A clinical photograph showing a skin lesion · a subject age 59 — 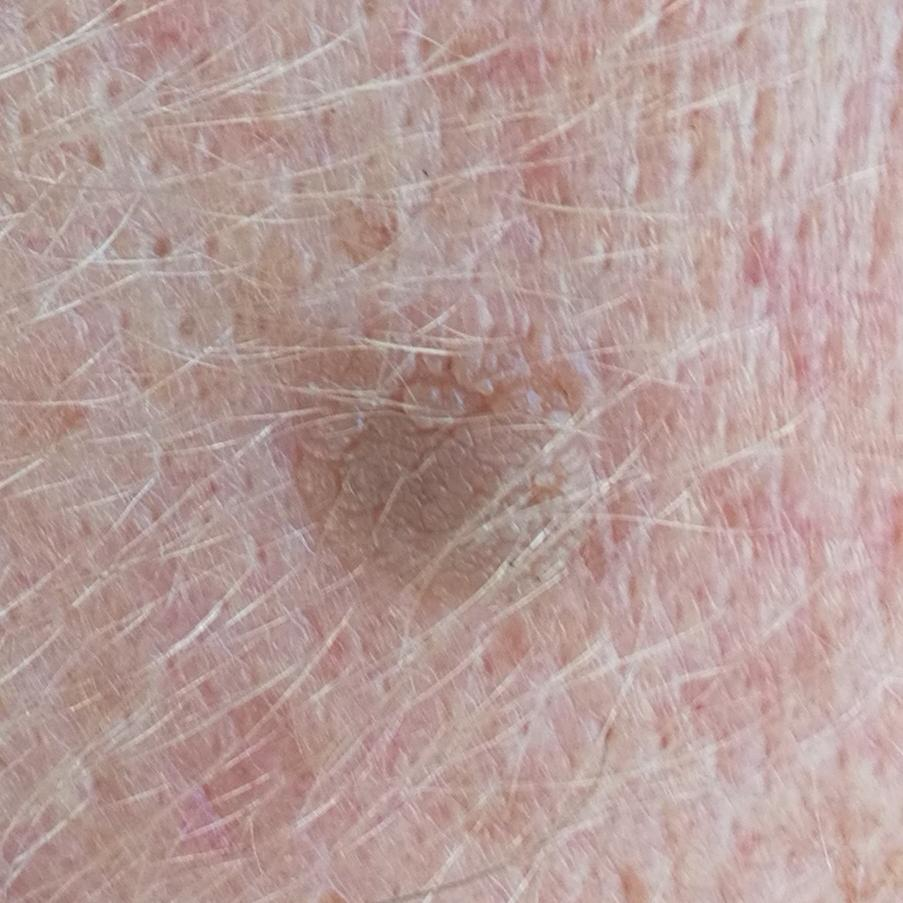The lesion is on the face. The patient reports that the lesion is elevated and has grown. The diagnostic impression was a seborrheic keratosis.